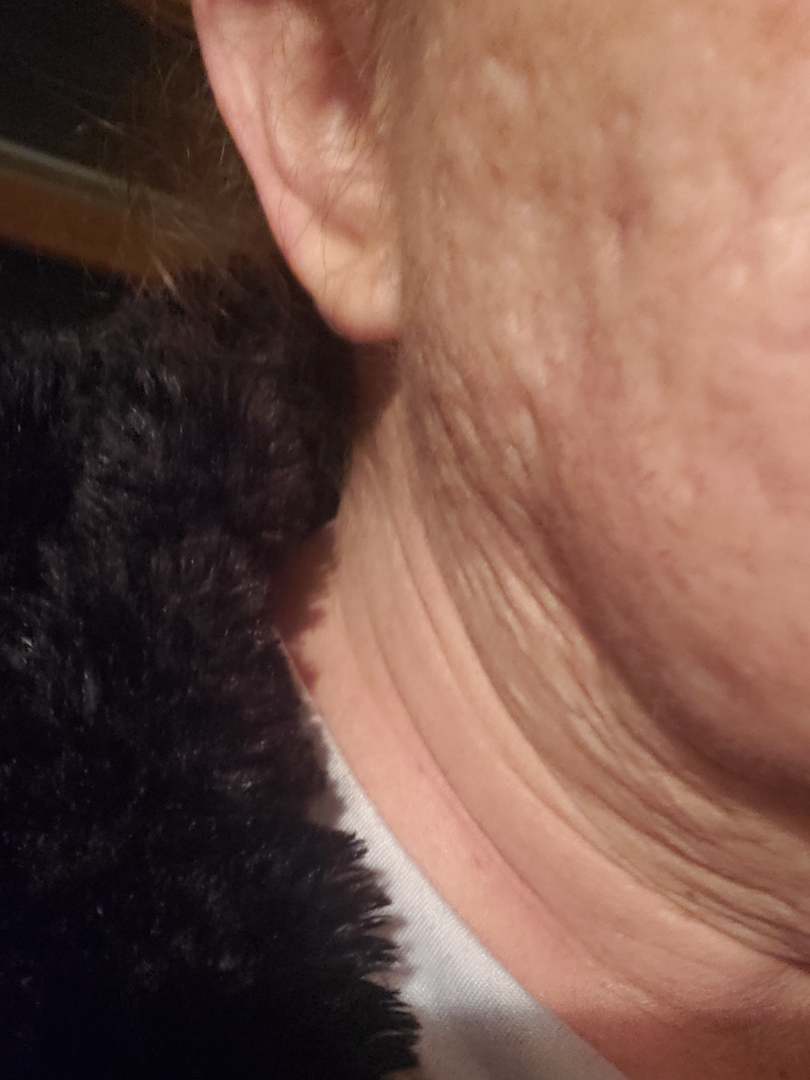On remote dermatologist review, the impression on review was Scar Condition.